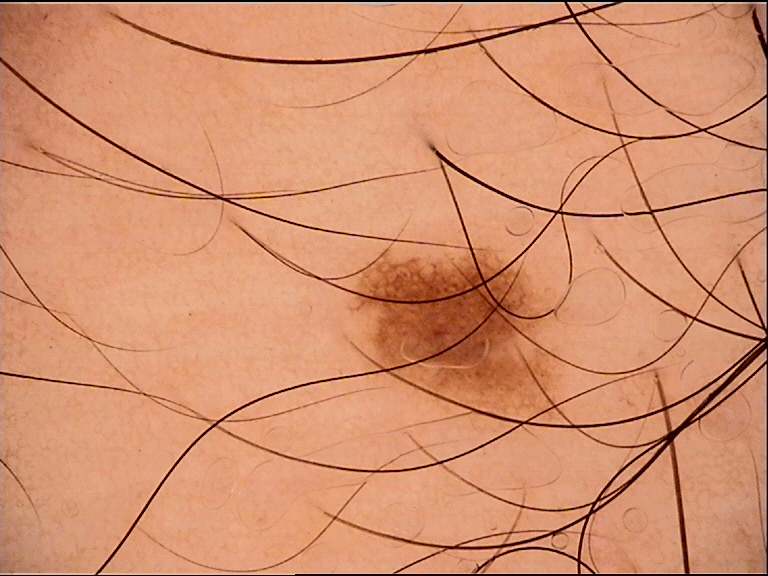image — dermatoscopy
diagnosis — junctional nevus (expert consensus)